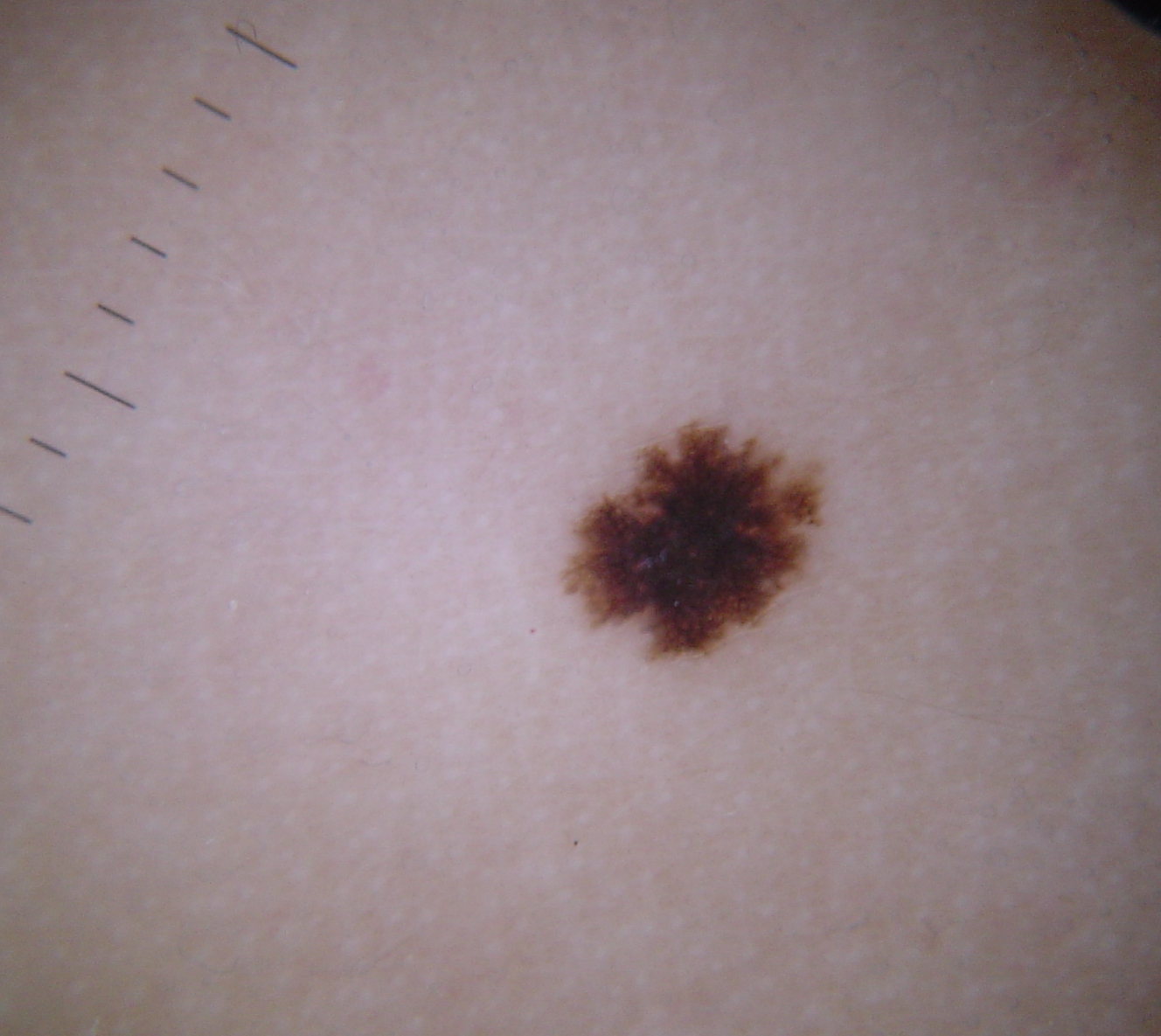A dermoscopic photograph of a skin lesion.
Classified as a dysplastic junctional nevus.